A skin lesion imaged with a dermatoscope: 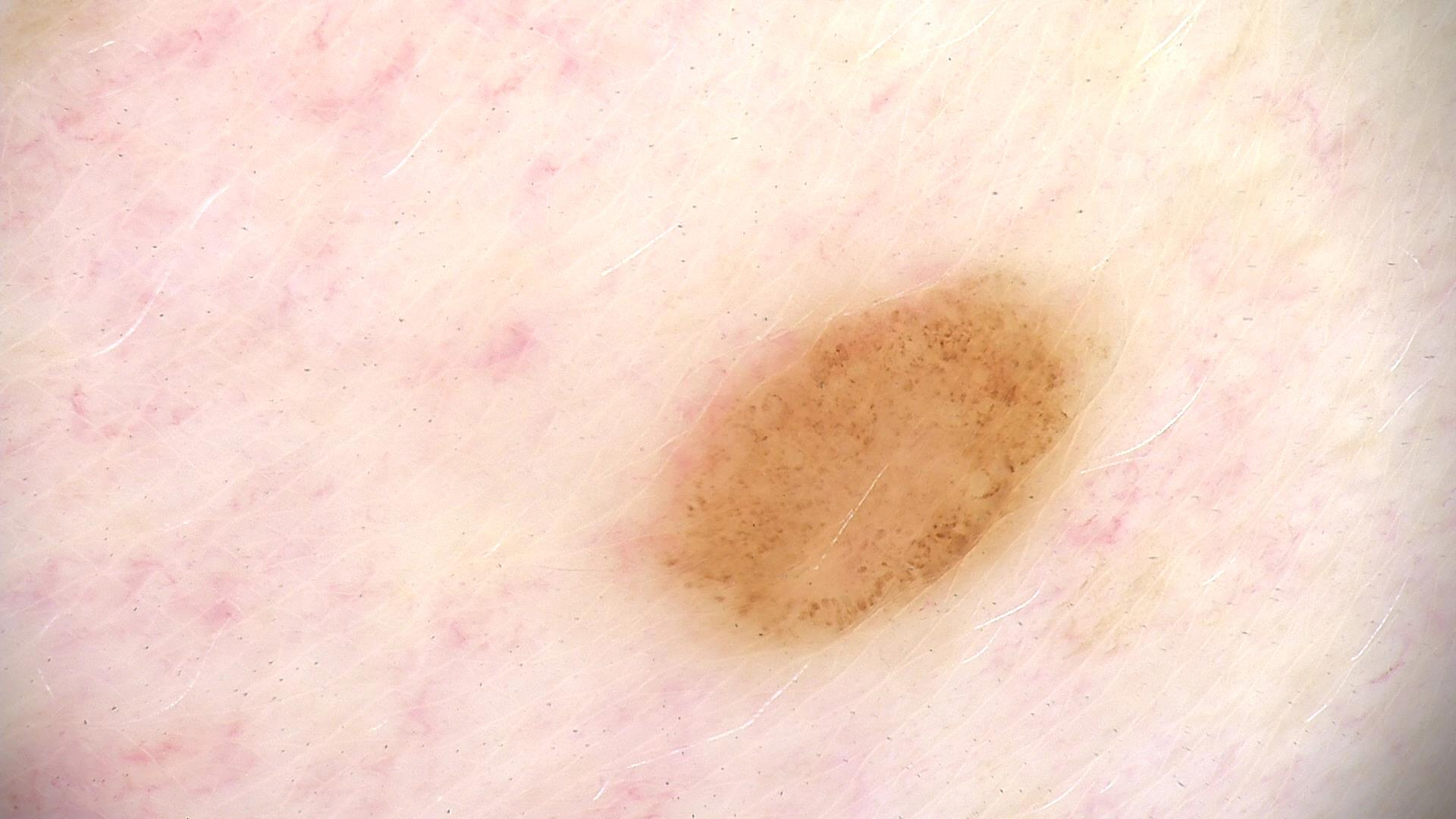Consistent with a benign lesion — a dysplastic junctional nevus.